A skin lesion imaged with a dermatoscope.
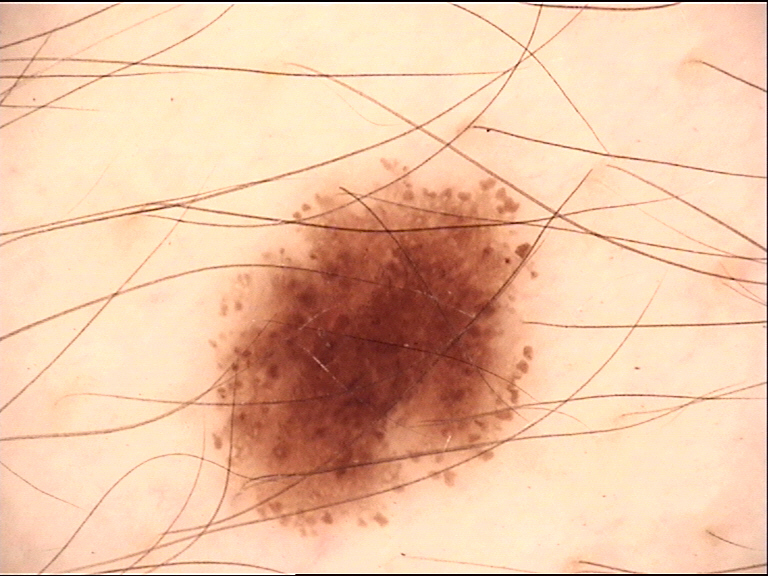Q: What is this lesion?
A: dysplastic junctional nevus (expert consensus)